An image taken at an angle; the lesion involves the leg:
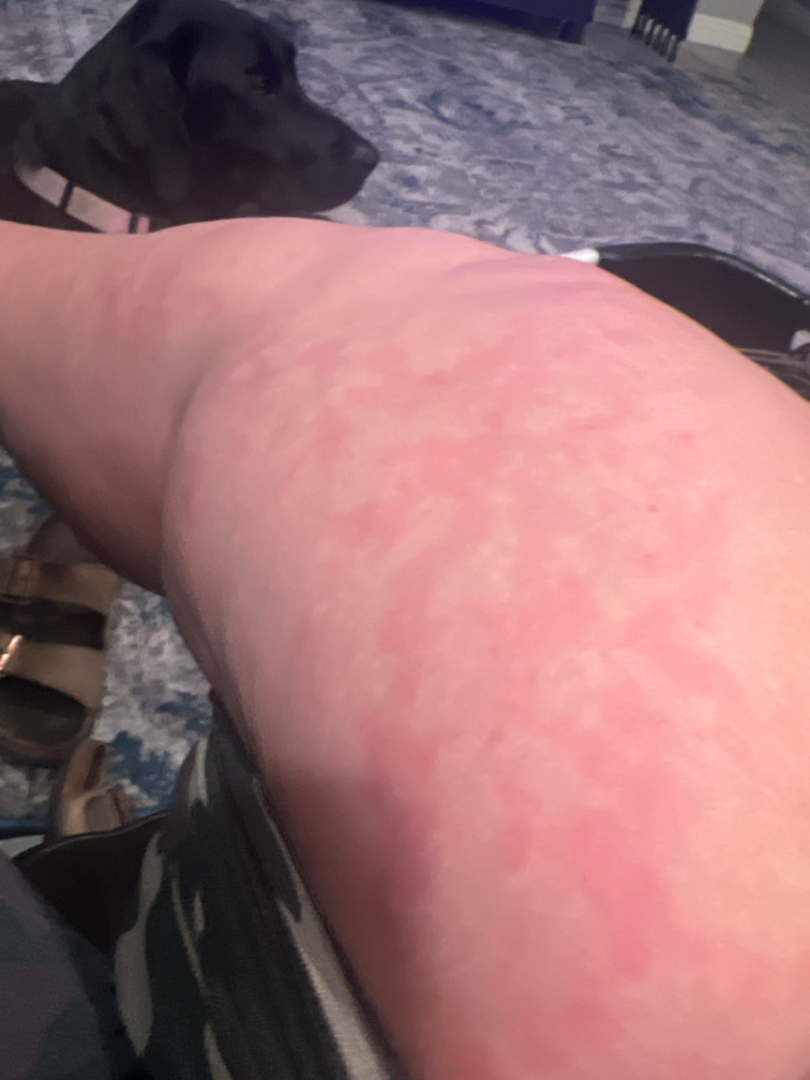assessment: indeterminate, reported symptoms: itching, constitutional symptoms: none reported, patient's own categorization: a rash, skin tone: Fitzpatrick skin type II; human graders estimated Monk skin tone scale 2 or 3 (two reviewer pools), present for: about one day, surface texture: flat.